The photograph is a close-up of the affected area · the leg is involved · the patient is 18–29, female.
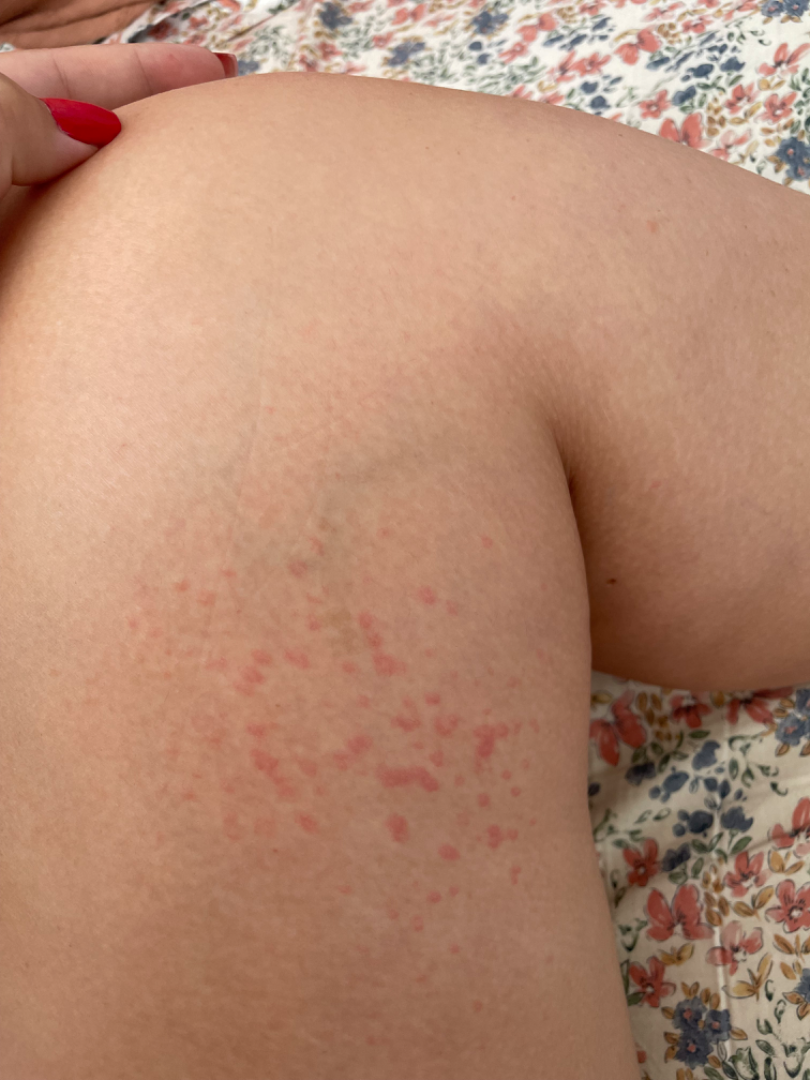Most likely Urticaria.